A skin lesion imaged with a dermatoscope.
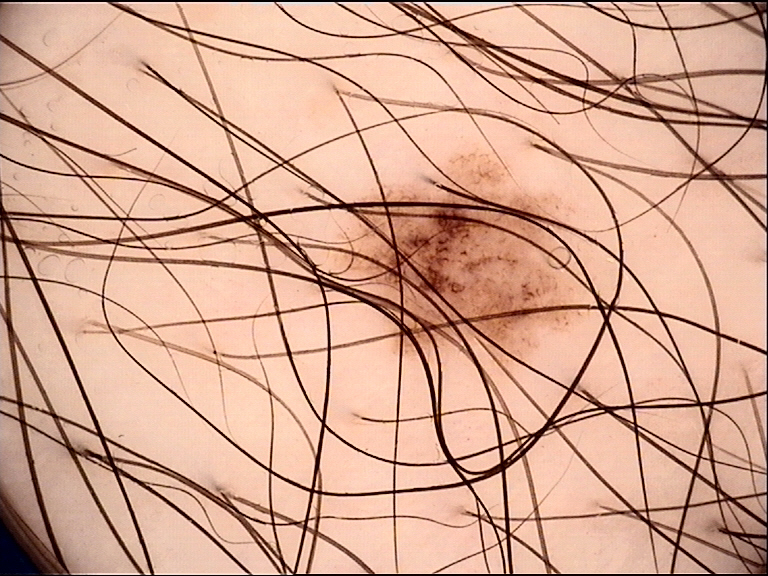Impression: The diagnostic label was a dysplastic junctional nevus.